The photograph was taken at a distance — 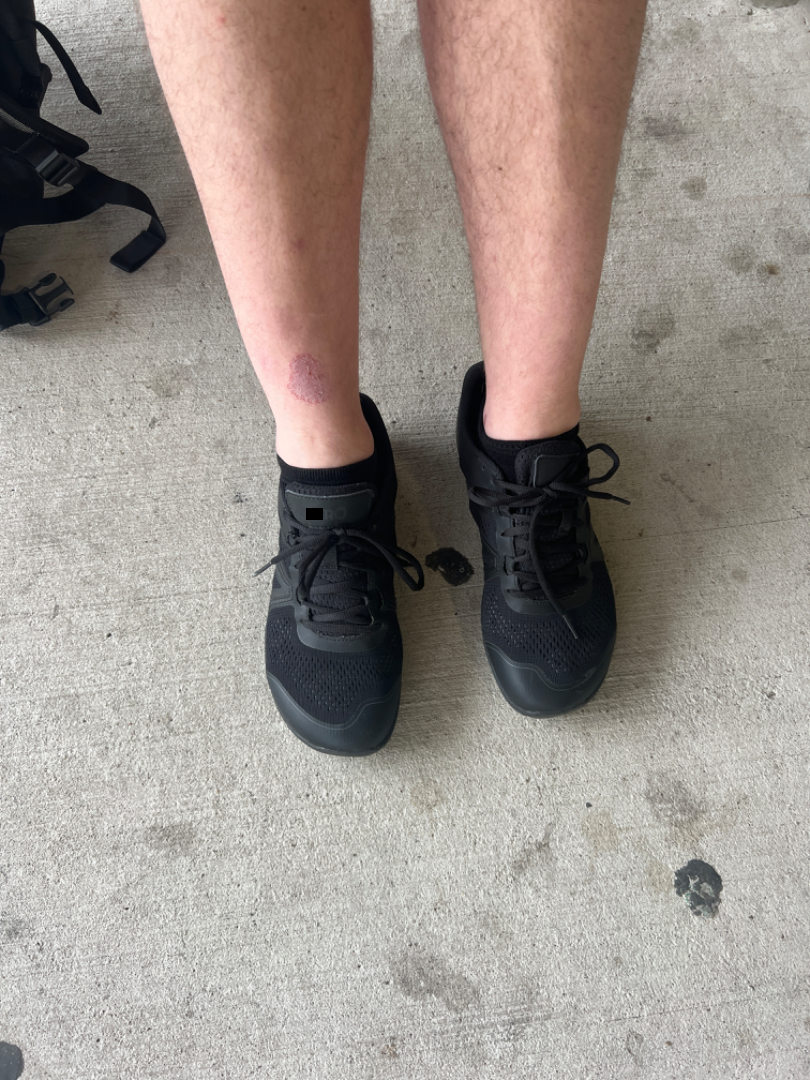differential:
  Eczema: 0.5
  Acute and chronic dermatitis: 0.5